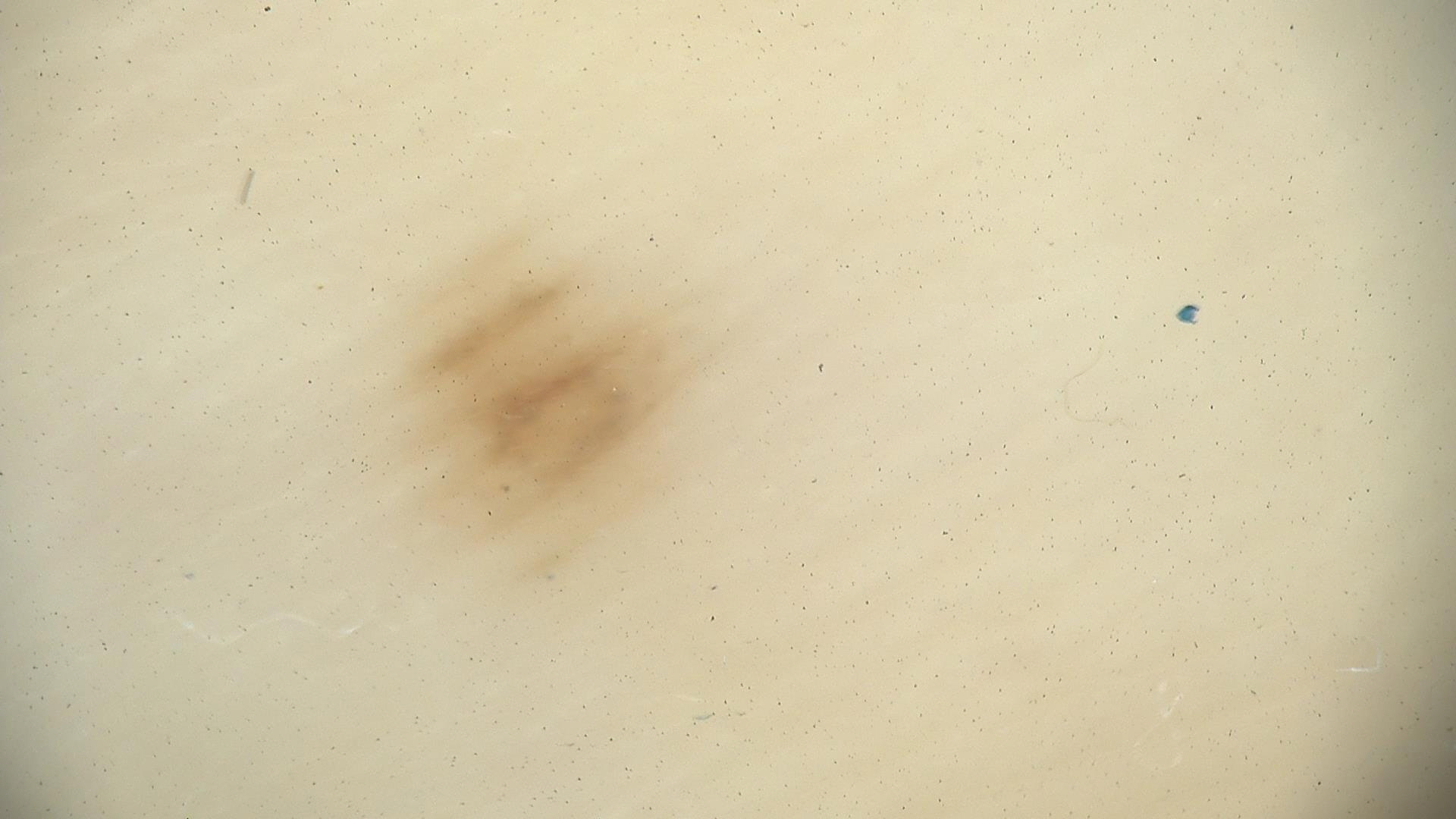<dermoscopy>
  <image>dermoscopy</image>
  <diagnosis>
    <name>acral junctional nevus</name>
    <code>ajb</code>
    <malignancy>benign</malignancy>
    <super_class>melanocytic</super_class>
    <confirmation>expert consensus</confirmation>
  </diagnosis>
</dermoscopy>